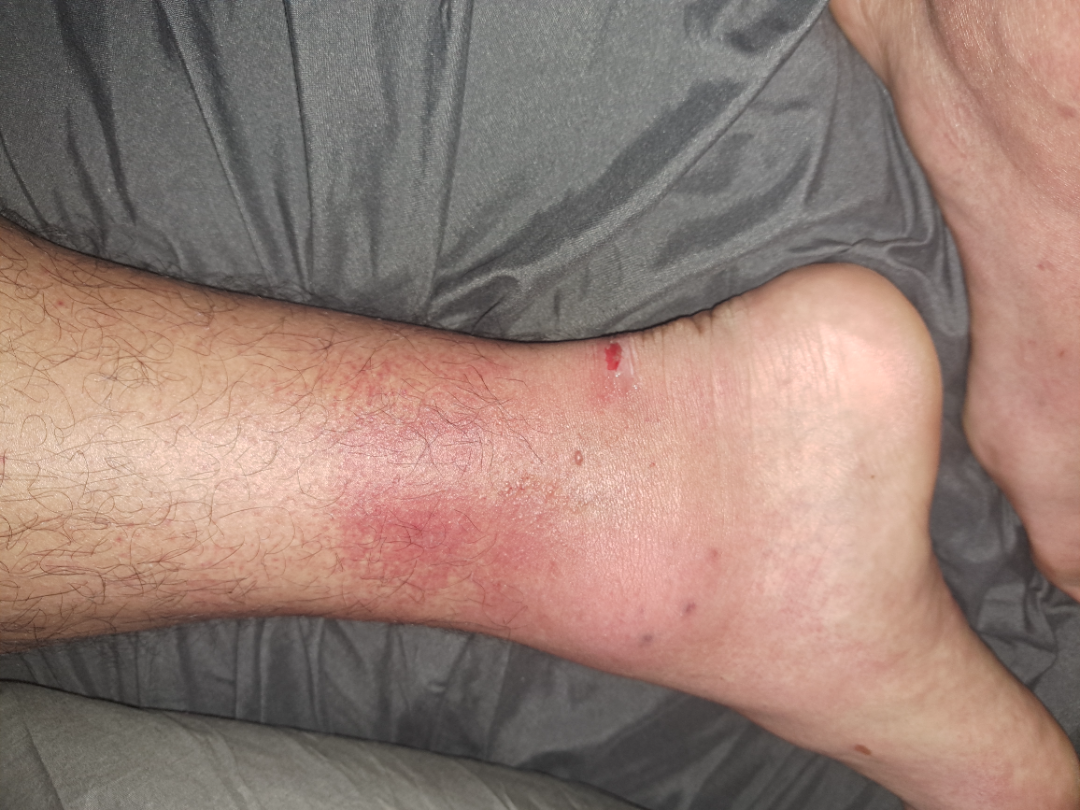The photo was captured at a distance. The arm, top or side of the foot and back of the hand are involved. The reviewing panel's impression was: Contact dermatitis (favored); Allergic Contact Dermatitis (considered); Insect Bite (considered); Acute generalised exanthematous pustulosis (considered).